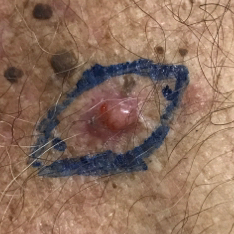• diagnostic label: basal cell carcinoma (biopsy-proven)